The subject is a female aged 30–39. Symptoms reported: itching. The patient indicates the condition has been present for less than one week. Close-up view. The lesion involves the arm and leg — 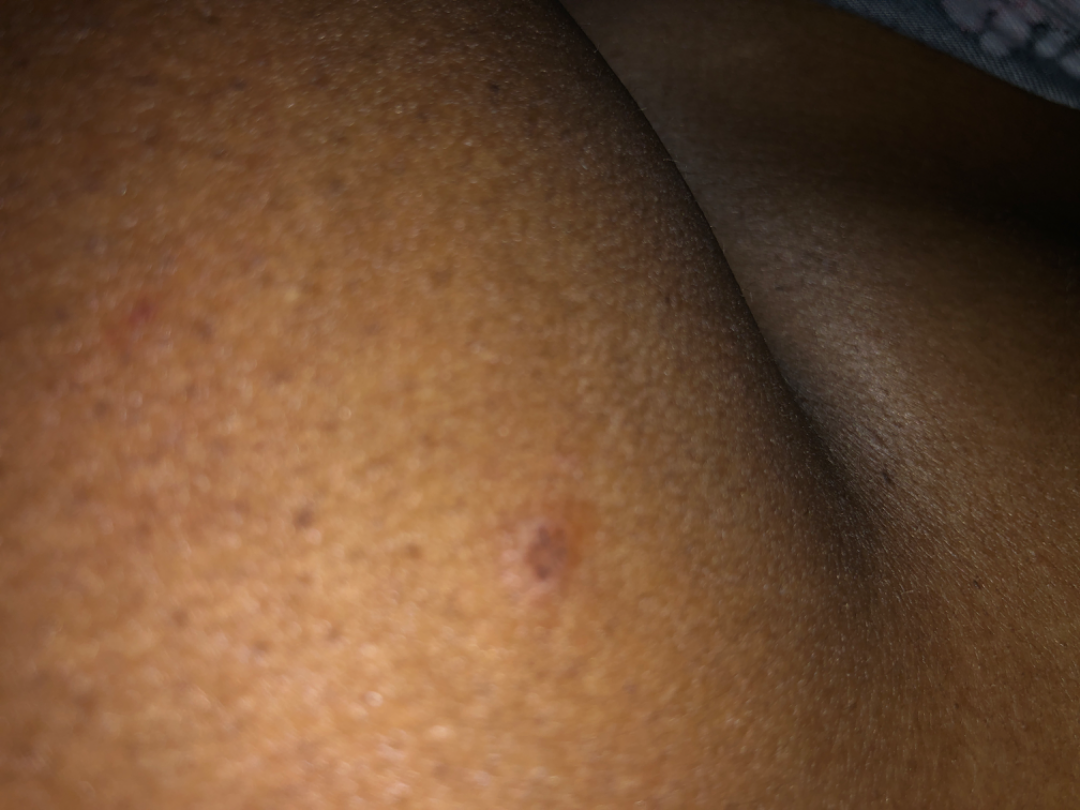The dermatologist could not determine a likely condition from the photograph alone.